The photograph was taken at a distance. The patient is a female aged 40–49. The leg, head or neck and arm are involved.
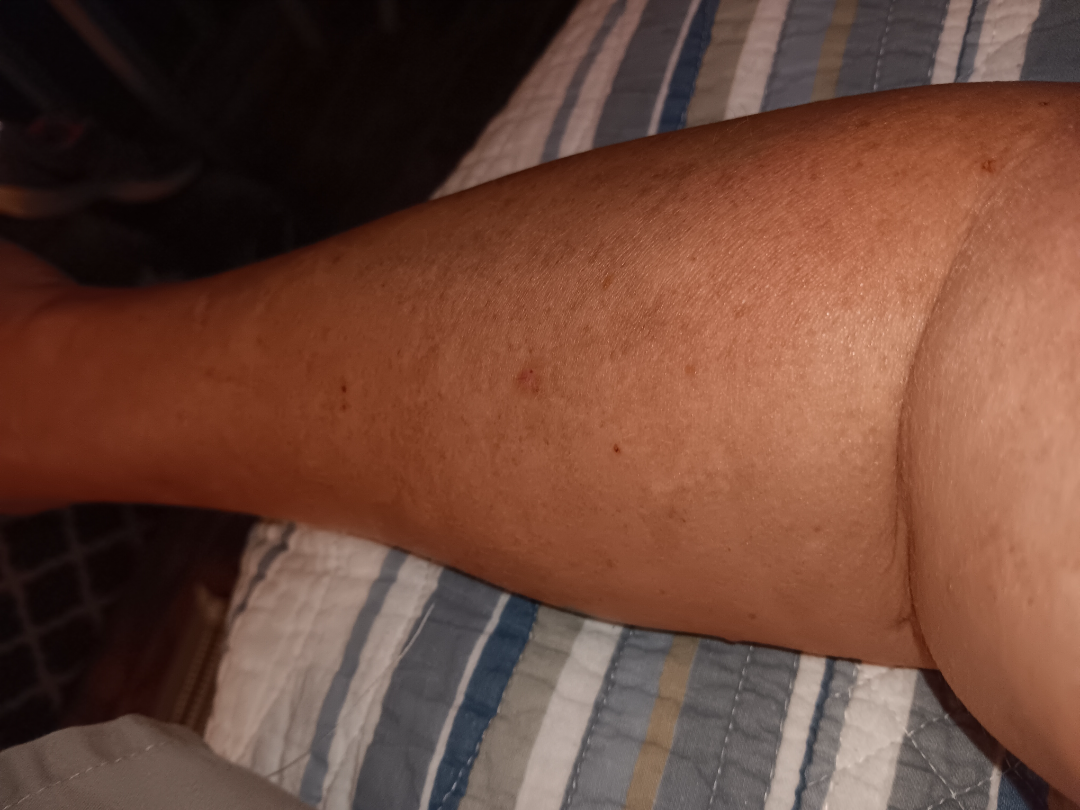| field | value |
|---|---|
| impression | three dermatologists each reviewed the case: the favored diagnosis is Actinic Keratosis; the differential also includes Herpes Zoster; an alternative is Eczema; less probable is Inflicted skin lesions; less likely is SCC/SCCIS |